A dermoscopic close-up of a skin lesion, the patient is a male aged 53 to 57: 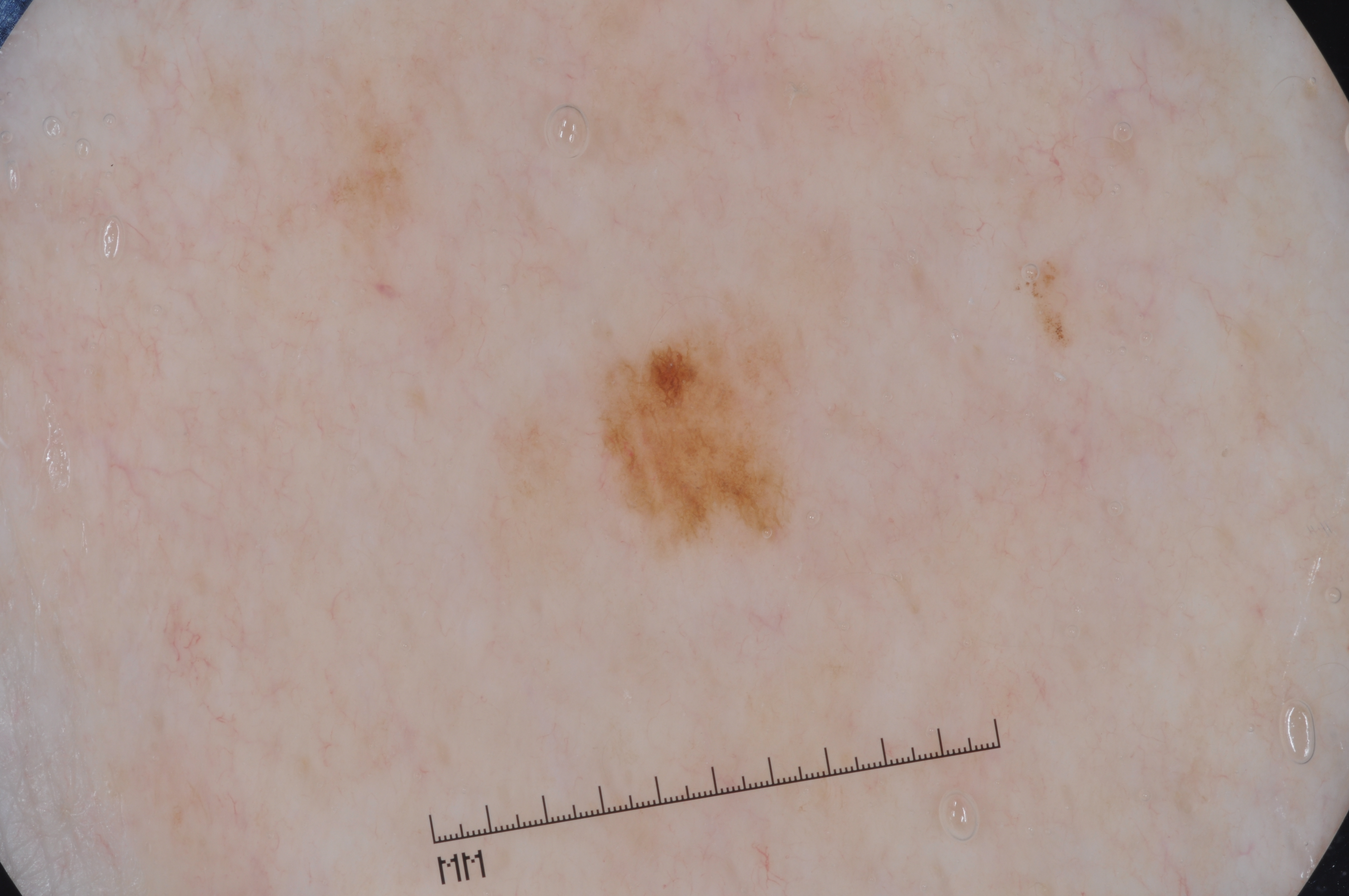Image and clinical context: As (left, top, right, bottom), the lesion is bounded by bbox(601, 329, 790, 539). Dermoscopy demonstrates pigment network, with no negative network, milia-like cysts, or streaks. Assessment: Diagnosed as a melanocytic nevus, a benign skin lesion.